A male patient aged 63-67. A wide-field clinical photograph of a skin lesion — 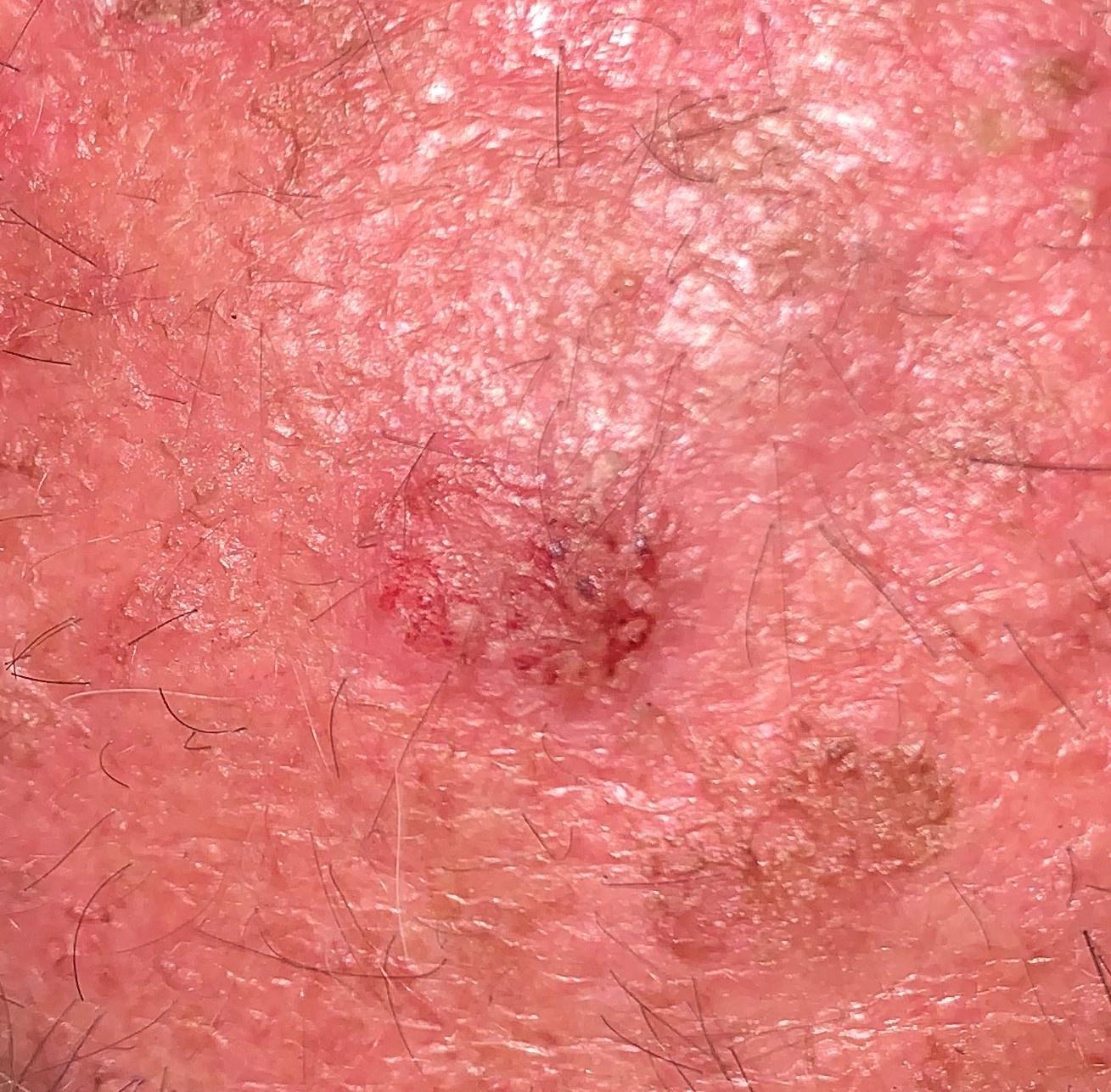The lesion is on the head or neck. Biopsy-confirmed as a solar or actinic keratosis.